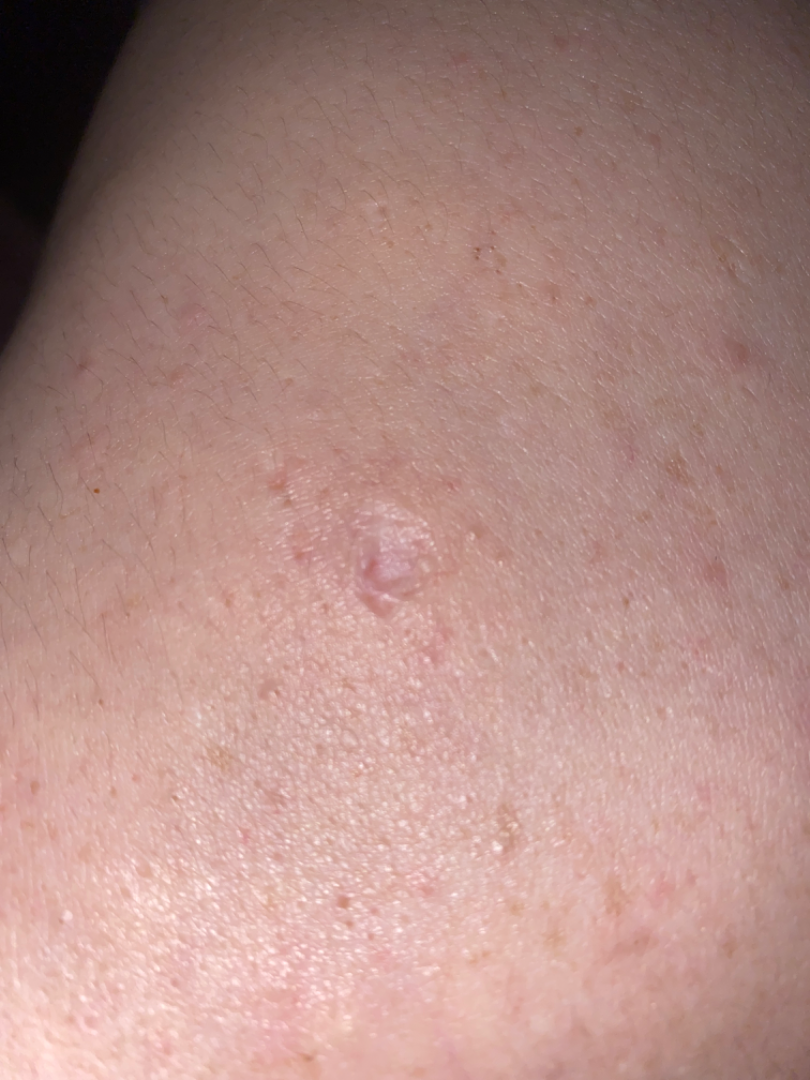Case summary:
• diagnostic considerations · Eczema (leading)